Close-up view · female subject, age 18–29 · the lesion involves the leg and top or side of the foot:
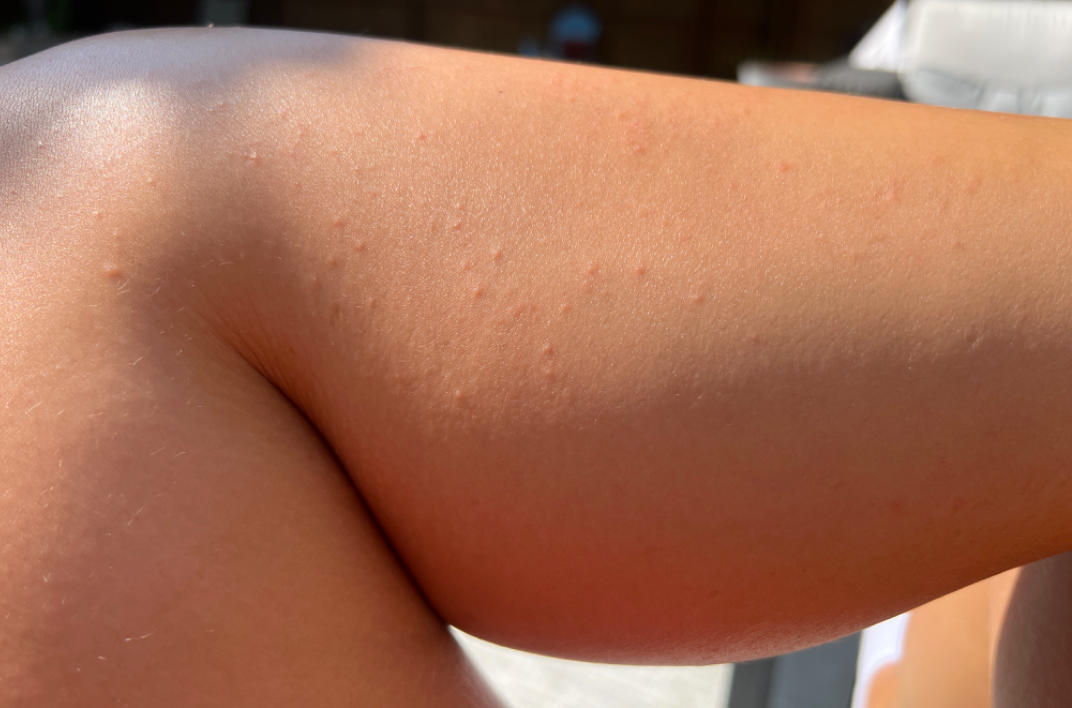clinical impression — in keeping with Folliculitis.